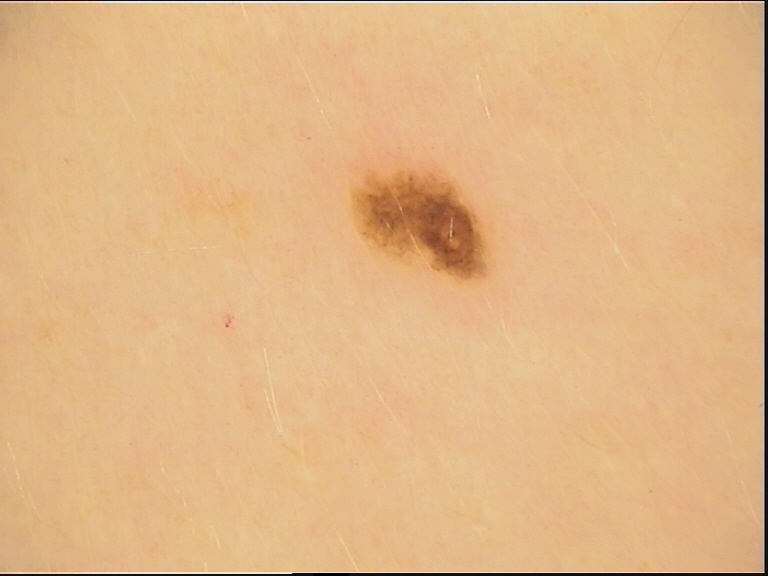Q: What is the imaging modality?
A: dermoscopy
Q: What was the diagnostic impression?
A: dysplastic junctional nevus (expert consensus)